A female subject roughly 85 years of age or older. The patient was assessed as FST II — 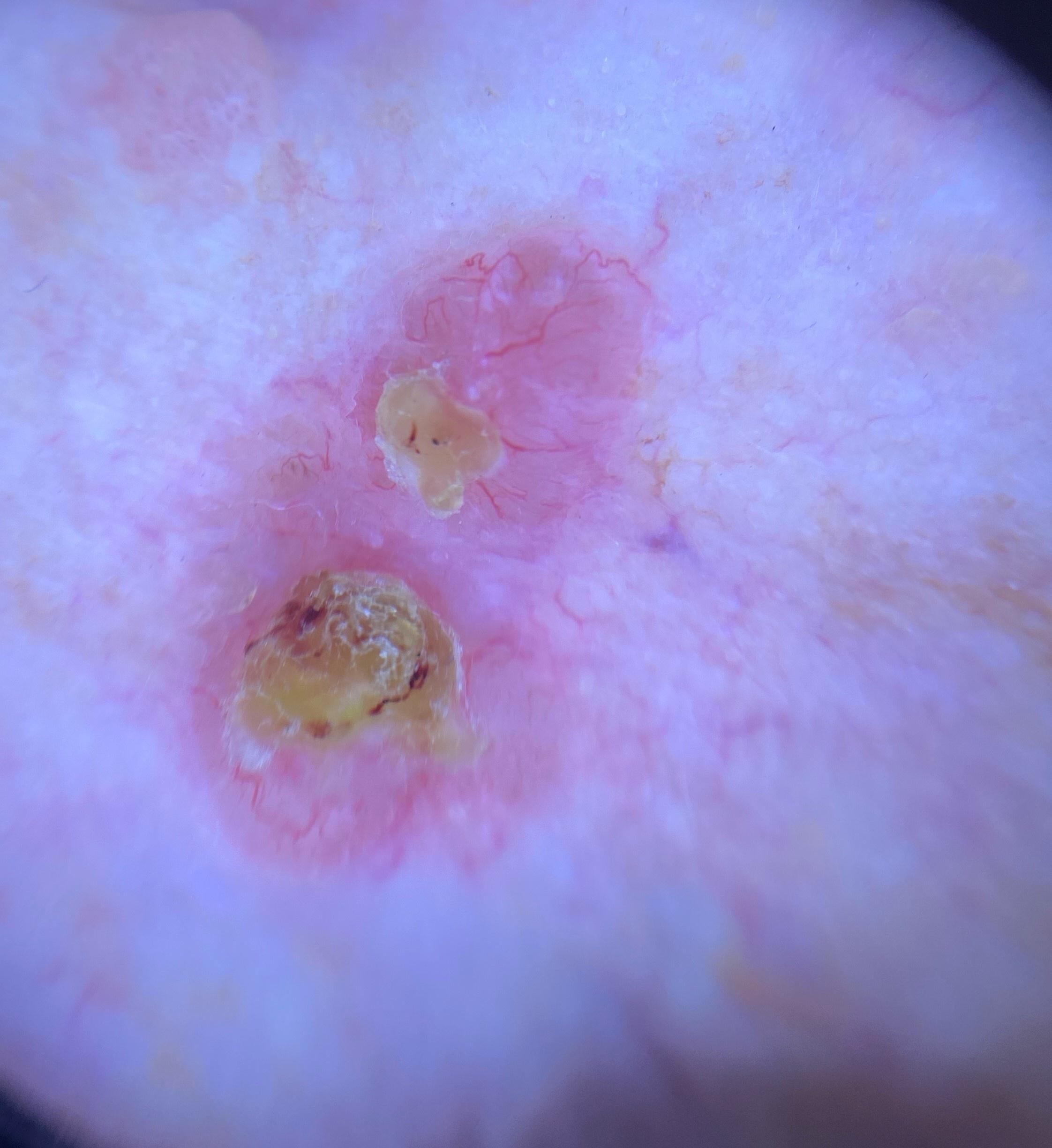<lesion>
<lesion_location>
<region>the head or neck</region>
</lesion_location>
<diagnosis>
<name>Basal cell carcinoma</name>
<malignancy>malignant</malignancy>
<confirmation>histopathology</confirmation>
<lineage>adnexal</lineage>
</diagnosis>
</lesion>